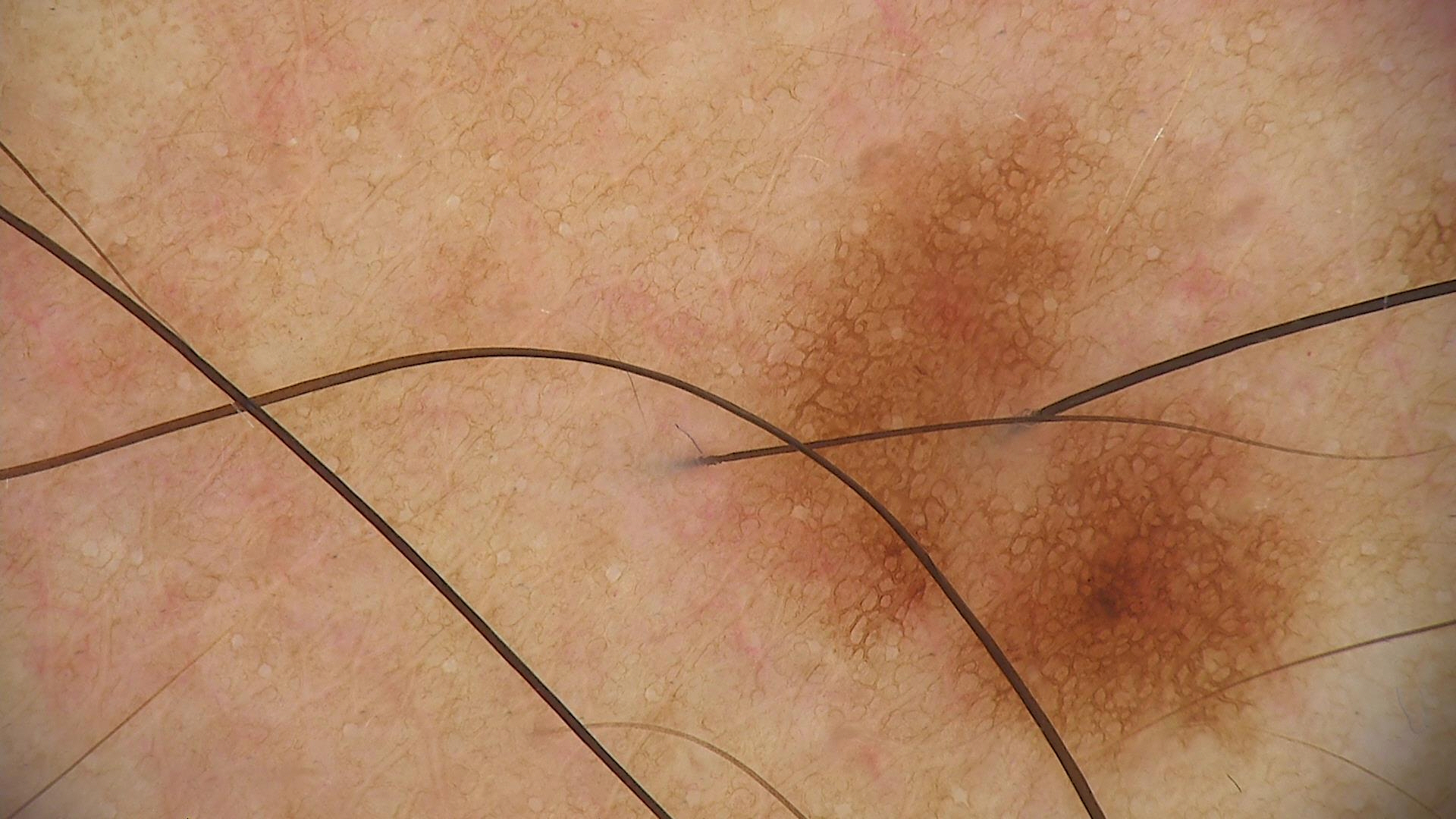{"image": "dermoscopy", "diagnosis": {"name": "dysplastic junctional nevus", "code": "jd", "malignancy": "benign", "super_class": "melanocytic", "confirmation": "expert consensus"}}